A skin lesion imaged with a dermatoscope: 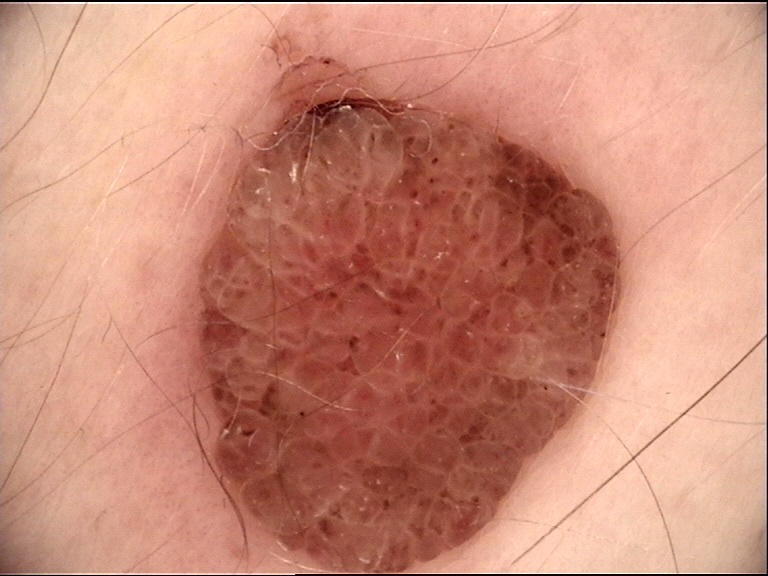The morphology is that of a banal lesion. Labeled as a dermal nevus.